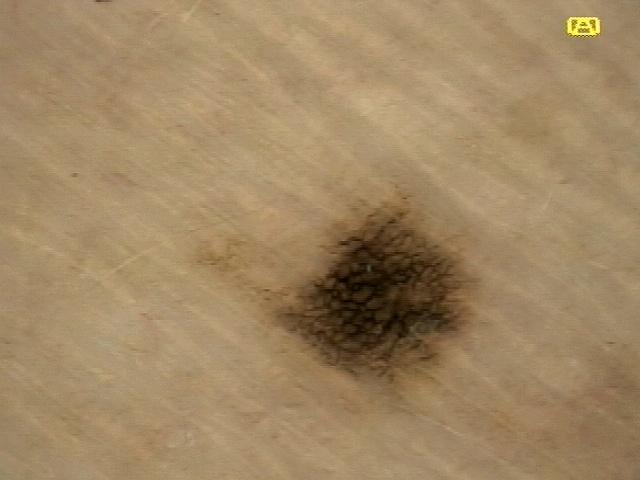Conclusion: The clinical assessment was a nevus.